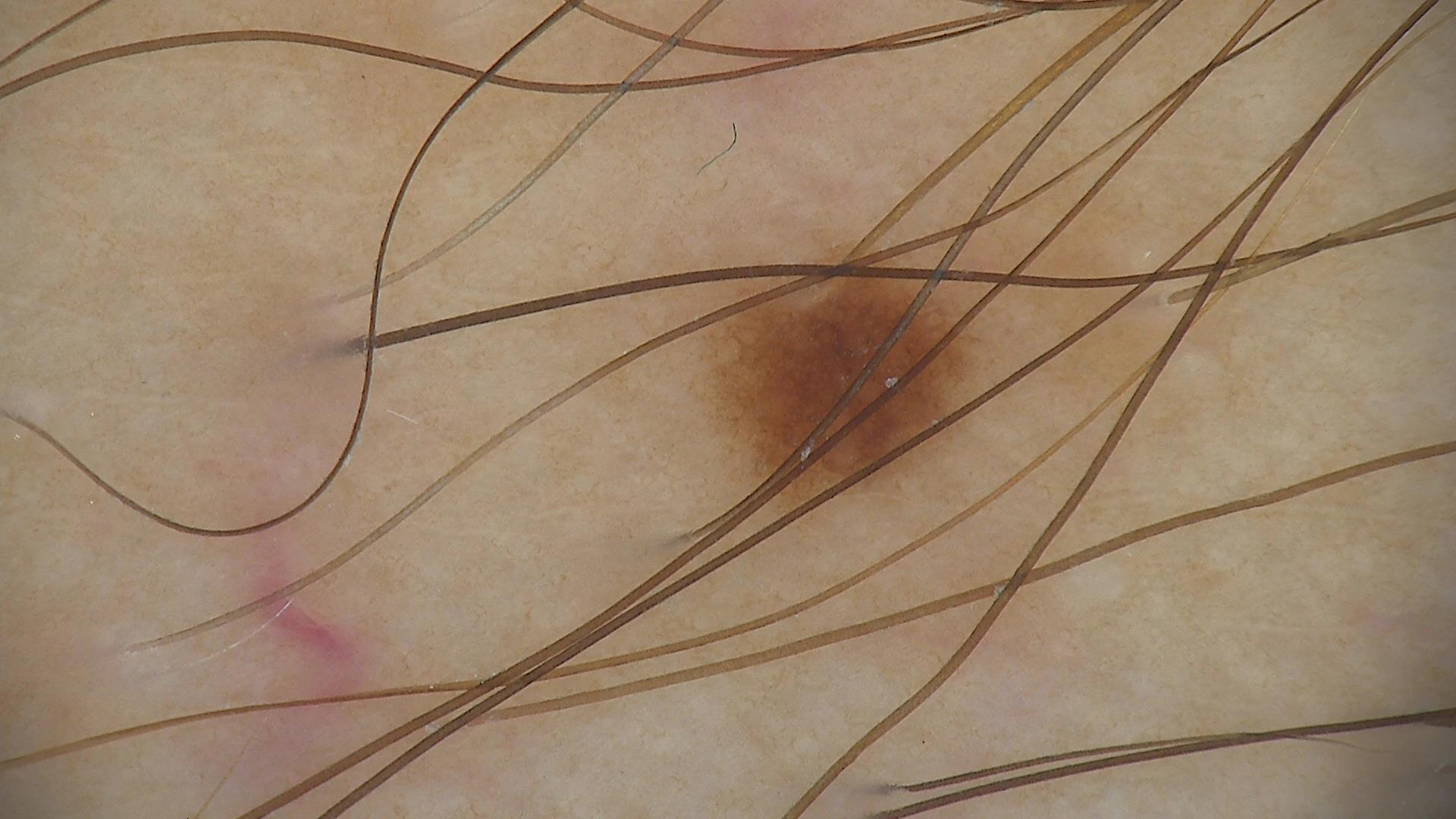Dermoscopy of a skin lesion. The diagnosis was a banal lesion — a junctional nevus.